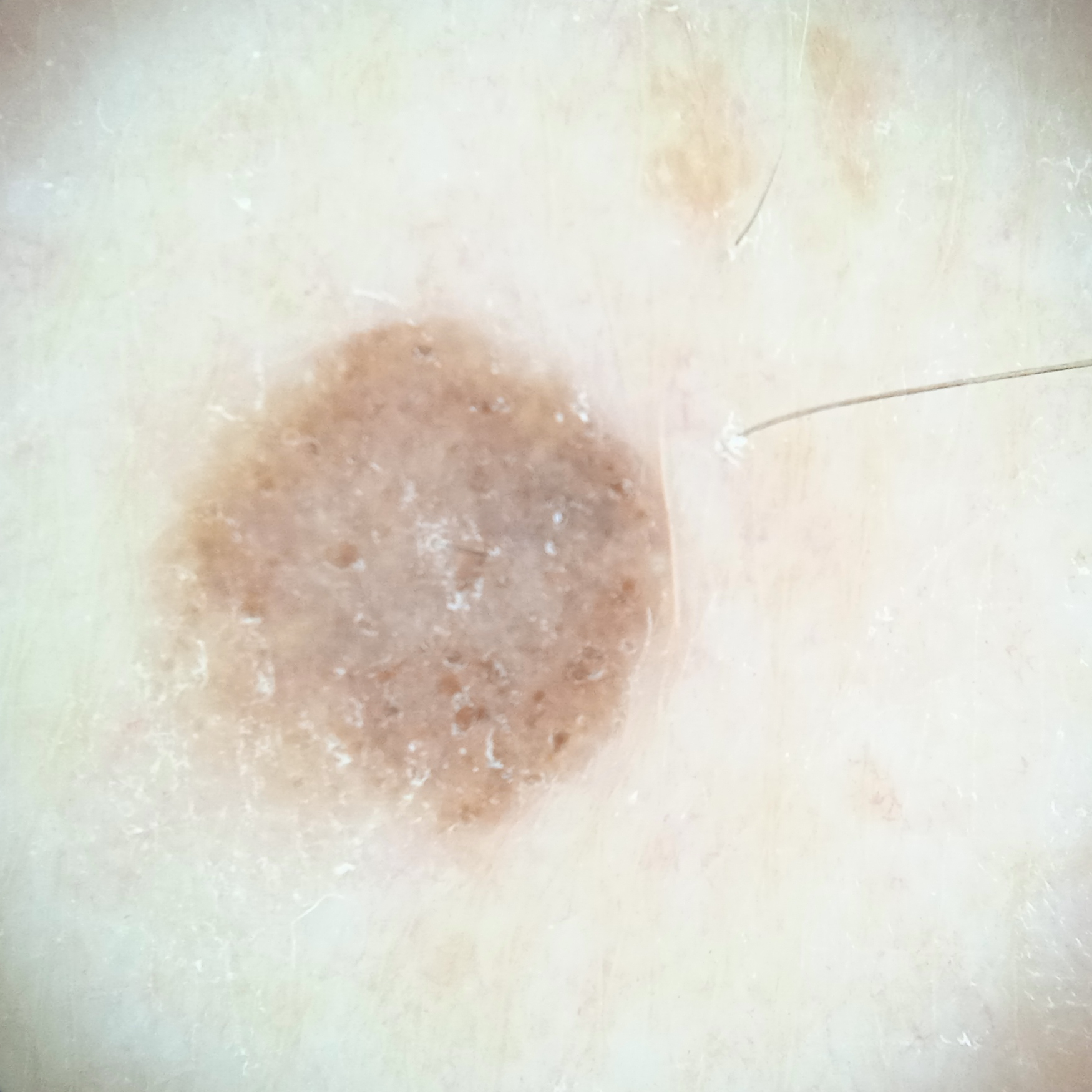nevus count: few melanocytic nevi overall
imaging: dermoscopy
sun reaction: skin tans without first burning
referral context: research study (no referral diagnosis)
diagnostic label: melanocytic nevus (dermatologist consensus)